The patient says their skin reddens painfully with sun exposure; a male patient aged 65; the patient describes having numerous moles; on a questionnaire the patient reported immunosuppression, a personal history of skin cancer, and a family history of skin cancer; a clinical photograph of a skin lesion: 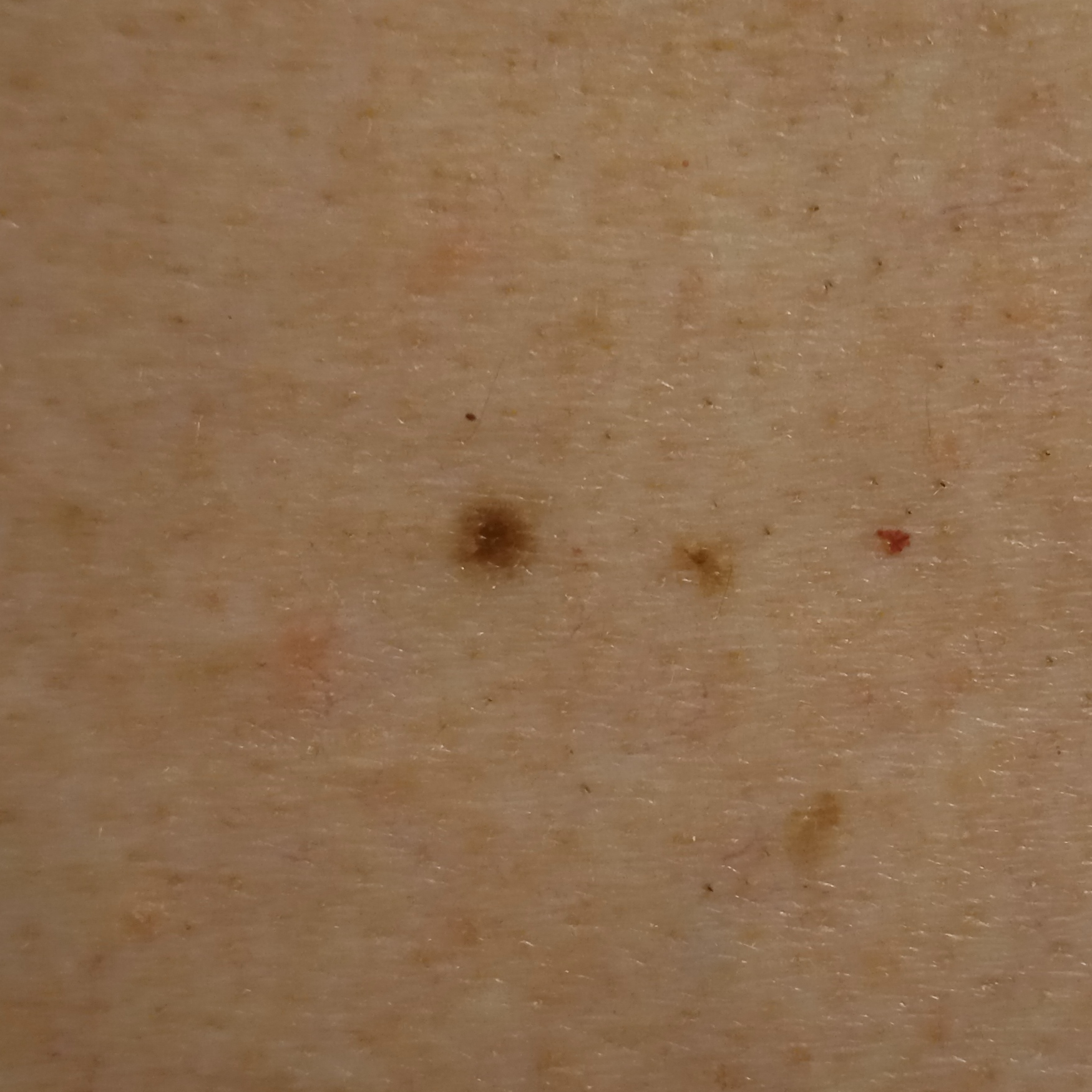The lesion involves the back. The lesion measures approximately 3.6 mm. Dermatologist review favored a melanocytic nevus.